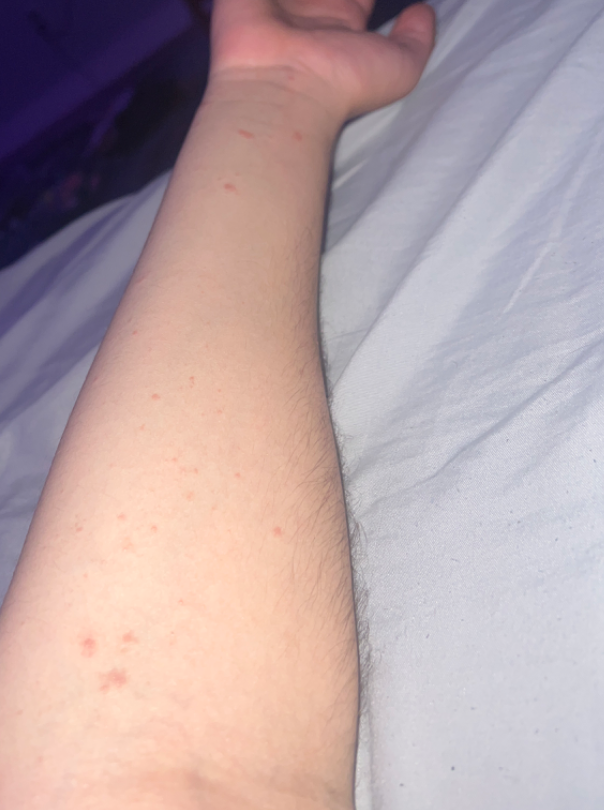The lesion involves the arm. The contributor is a male aged 18–29. The photograph was taken at an angle. On independent review by the dermatologists: the favored diagnosis is Allergic Contact Dermatitis; also on the differential is Lichen nitidus; less probable is Verruca vulgaris; a remote consideration is Molluscum Contagiosum.